Present for about one day, the patient indicates itching, this image was taken at an angle, the patient reported no systemic symptoms, the arm is involved, the patient indicates the lesion is flat: 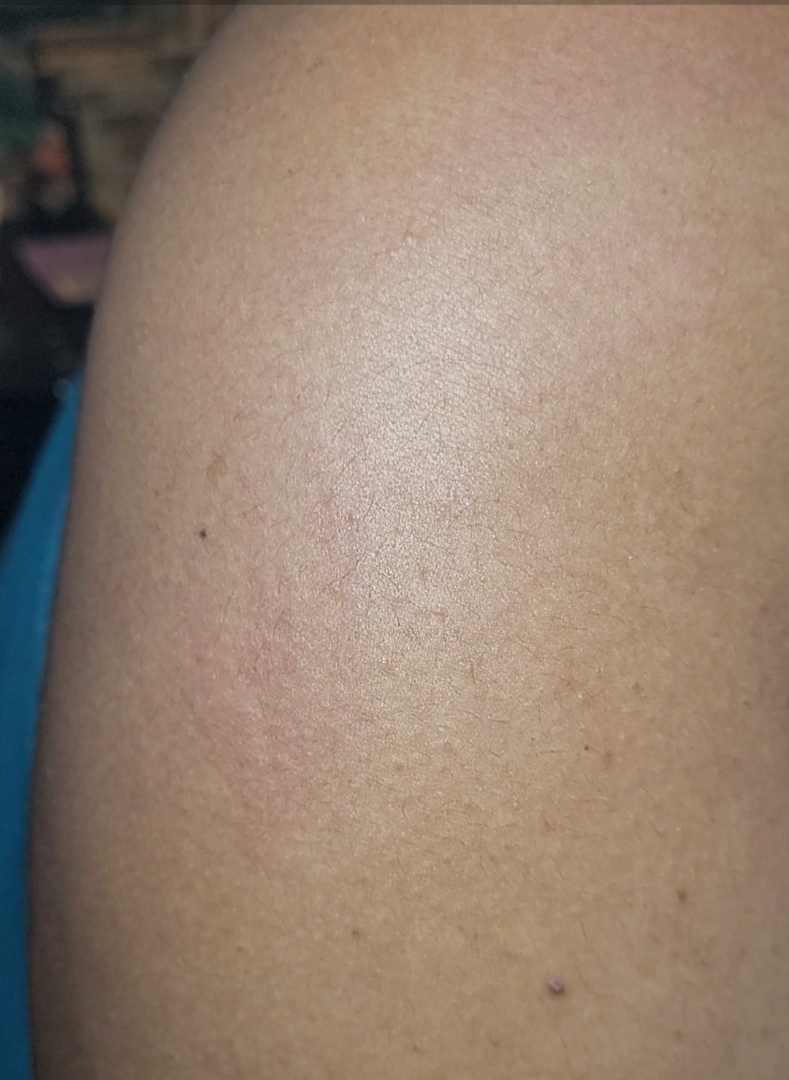Findings: The reviewing clinician's impression was: Urticaria (primary).